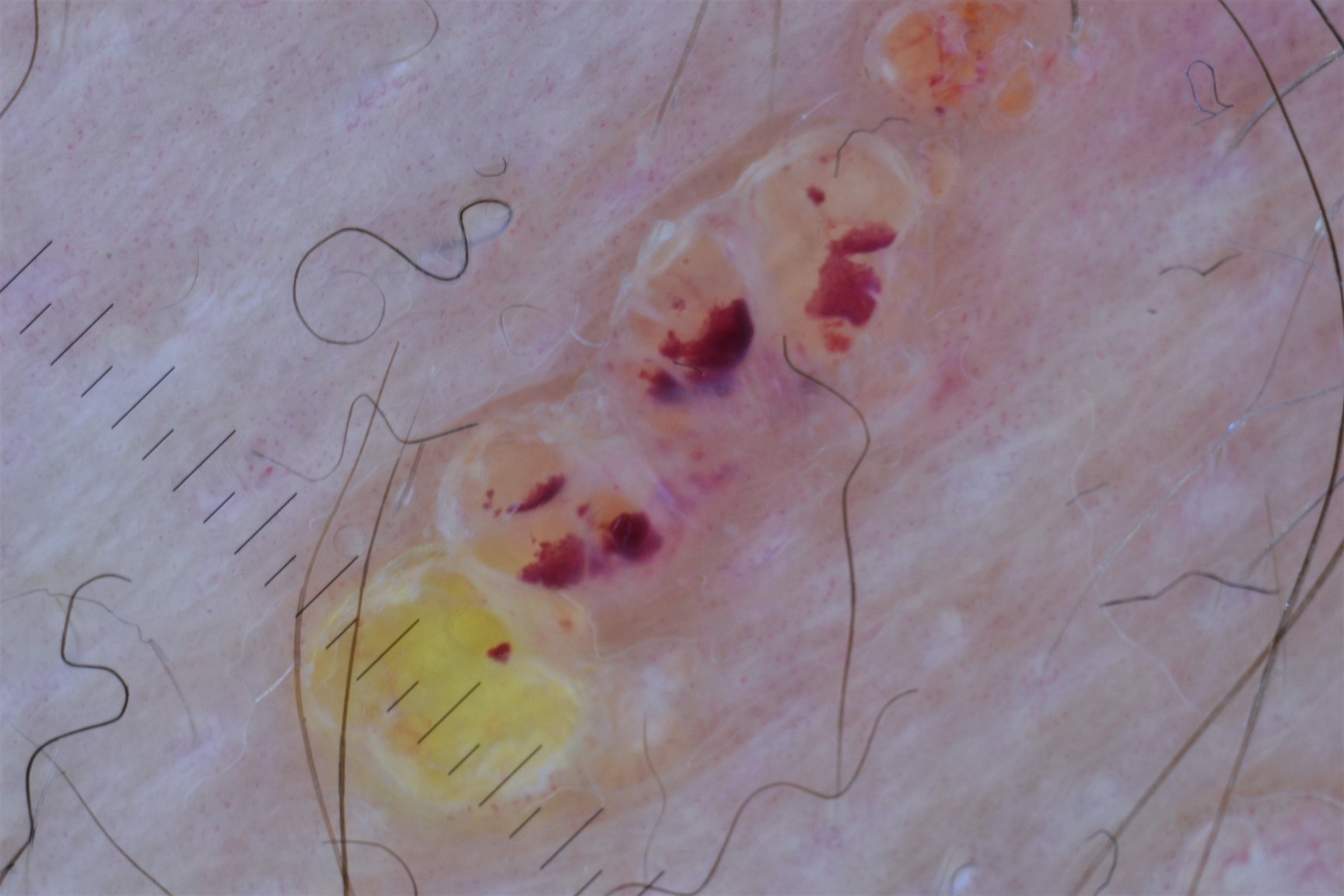This is a vascular lesion. The diagnostic label was a lymphangioma.